A dermoscopic view of a skin lesion.
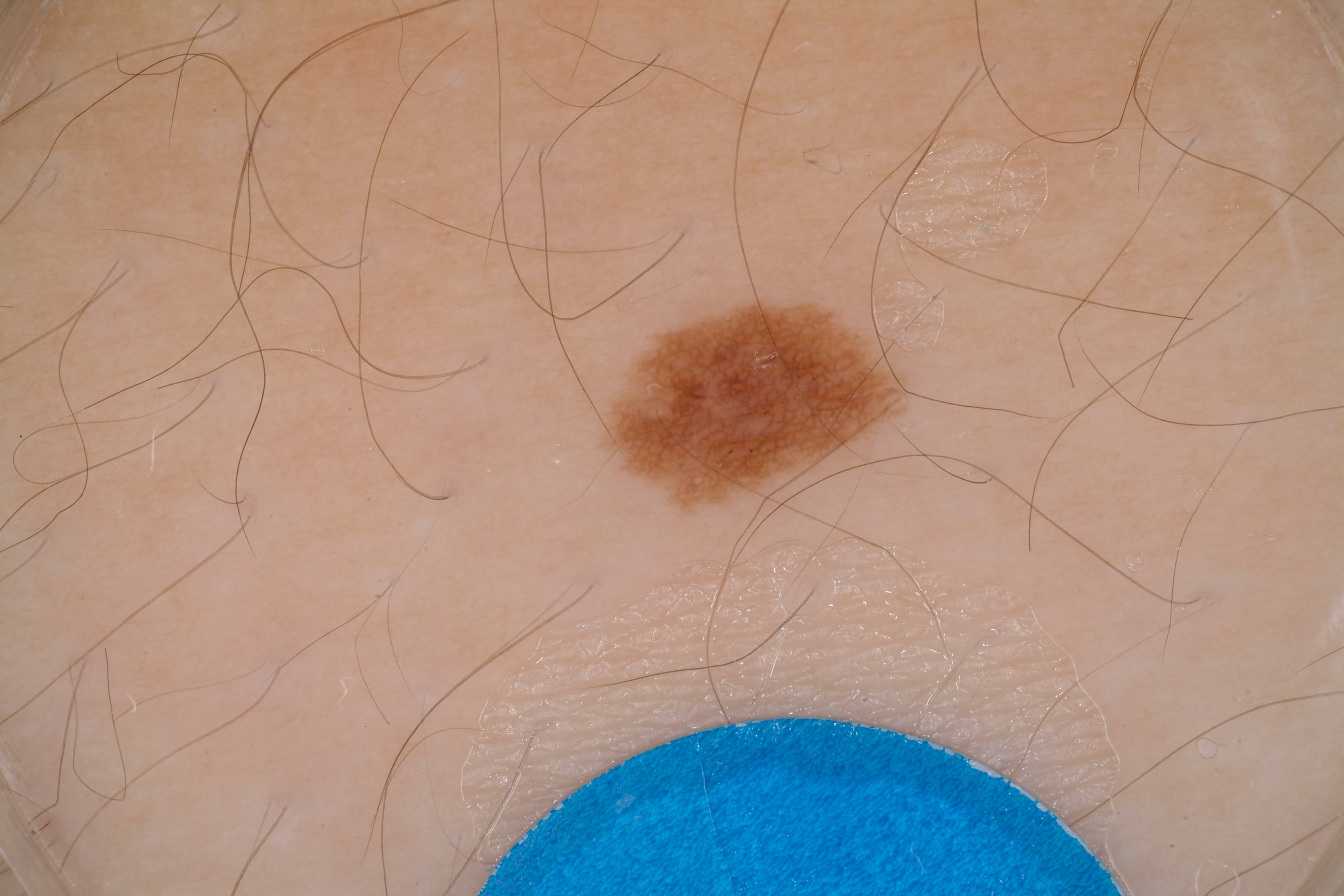As (left, top, right, bottom), the lesion is bounded by 606 283 911 514.
Dermoscopic examination shows pigment network; no milia-like cysts, negative network, or streaks.
The lesion was assessed as a melanocytic nevus.